This image was taken at an angle, the head or neck is involved: 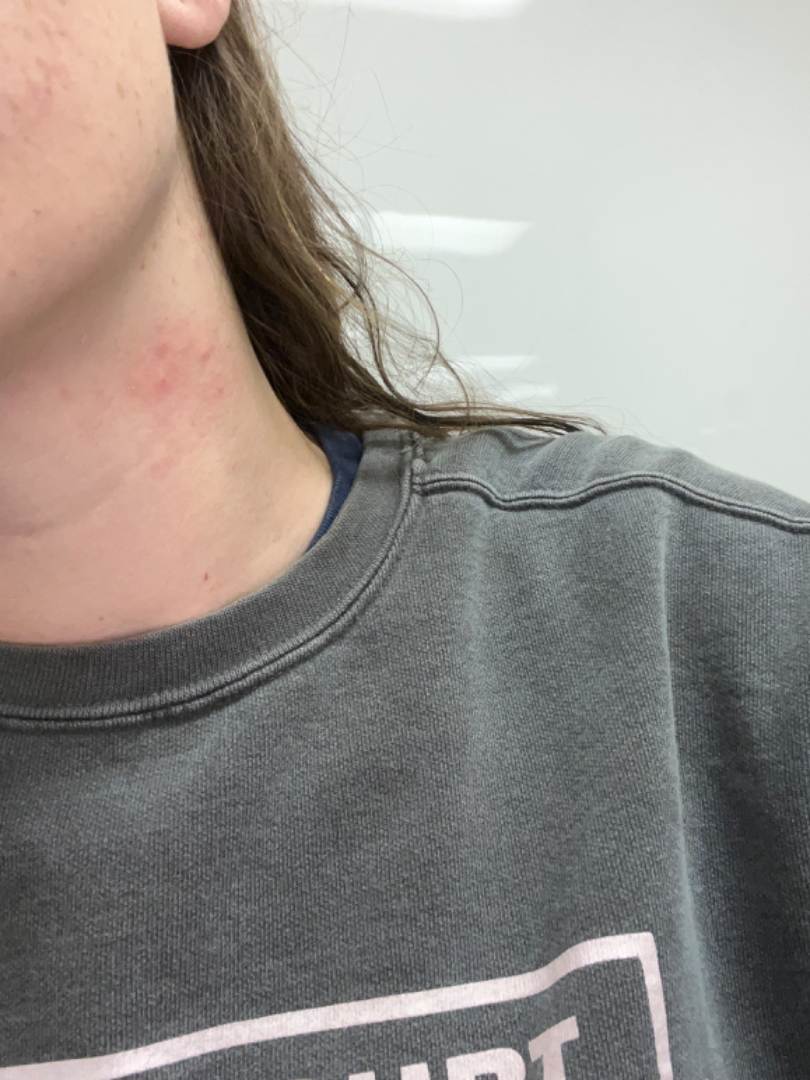On remote review of the image: the differential is split between Allergic Contact Dermatitis and Irritant Contact Dermatitis.